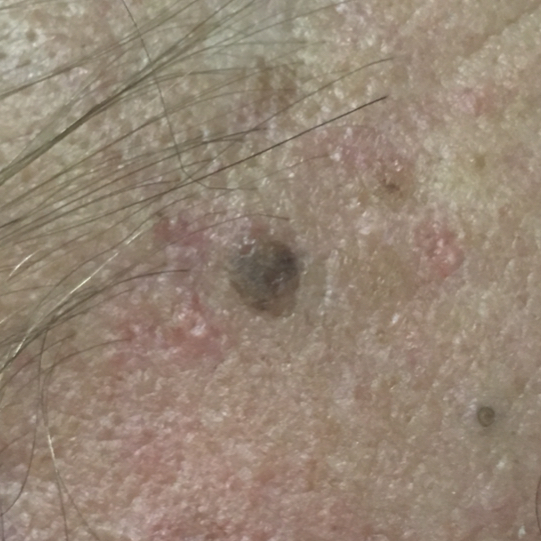image type: smartphone clinical photo | patient: 59 years of age | body site: the face | symptoms: itching, growth | diagnosis: seborrheic keratosis (clinical consensus).